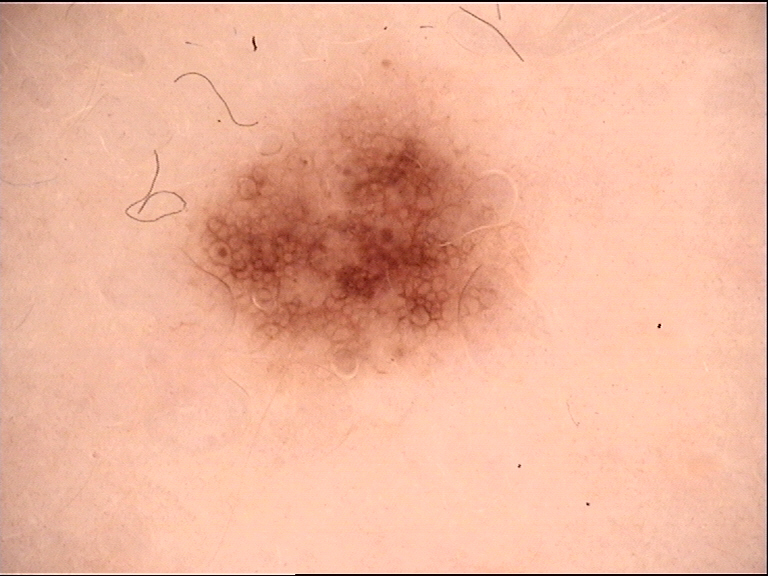Findings:
• class · dysplastic junctional nevus (expert consensus)